A dermoscopy image of a skin lesion; collected as part of a research study, without a referral diagnosis; a female subject 50 years of age.
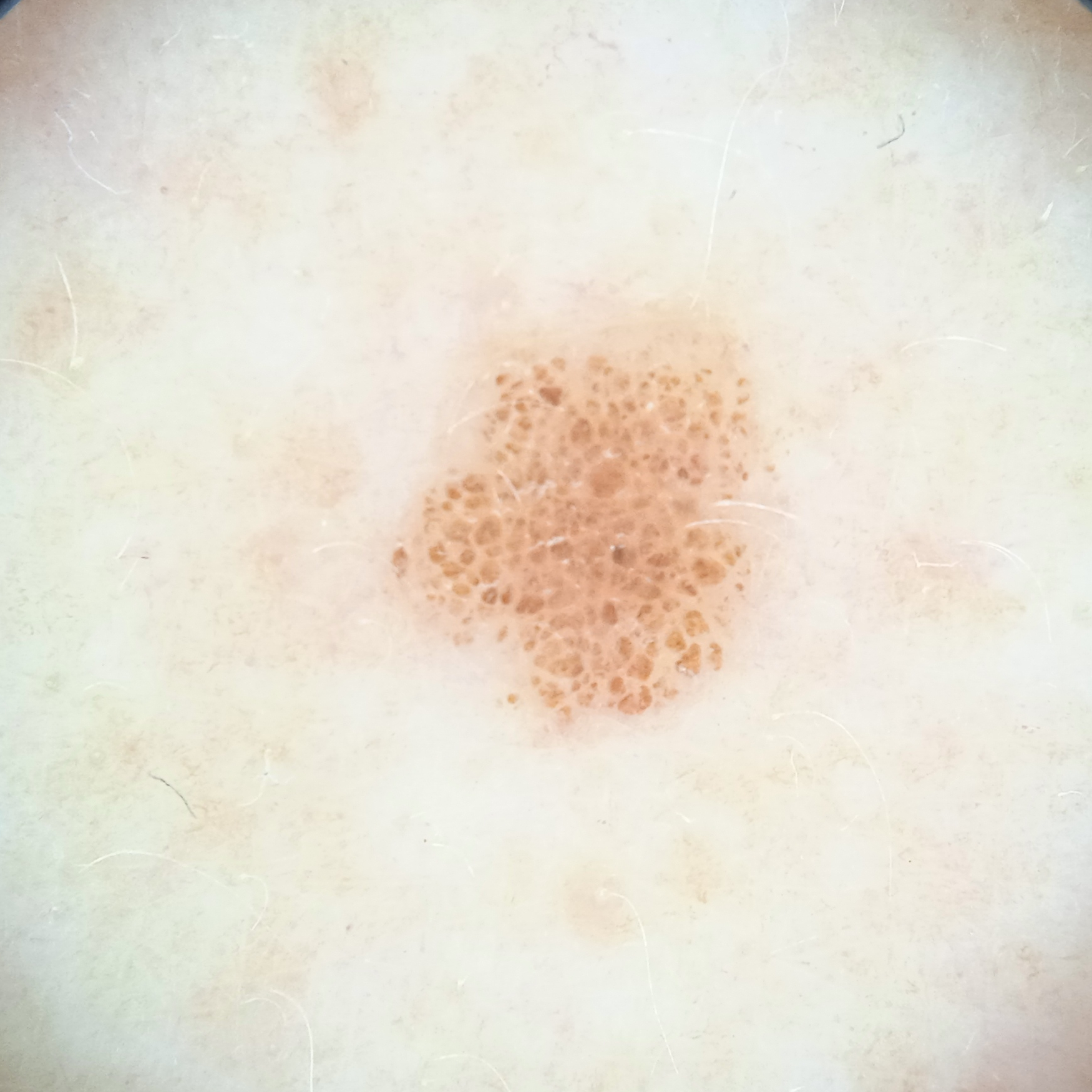The lesion is located on the back.
The lesion is about 5.1 mm across.
The diagnostic impression was a melanocytic nevus.